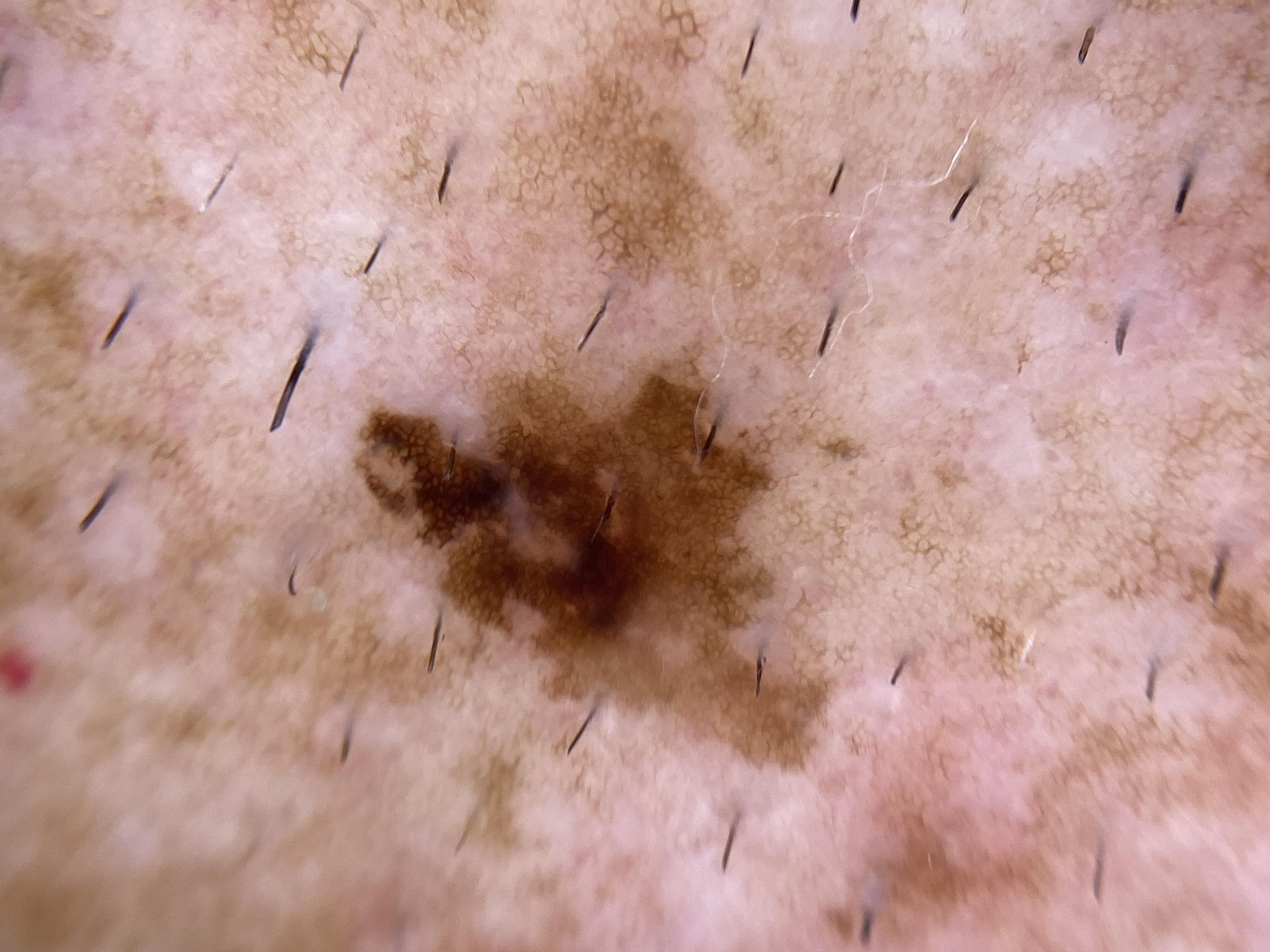FST: II; patient: male, aged approximately 55; location: the trunk, specifically the posterior trunk; diagnostic label: Nevus (biopsy-proven).